A female subject 50 years old. The patient describes having a moderate number of moles. The patient says their skin reddens painfully with sun exposure. By self-report, no immunosuppression and no family history of skin cancer.
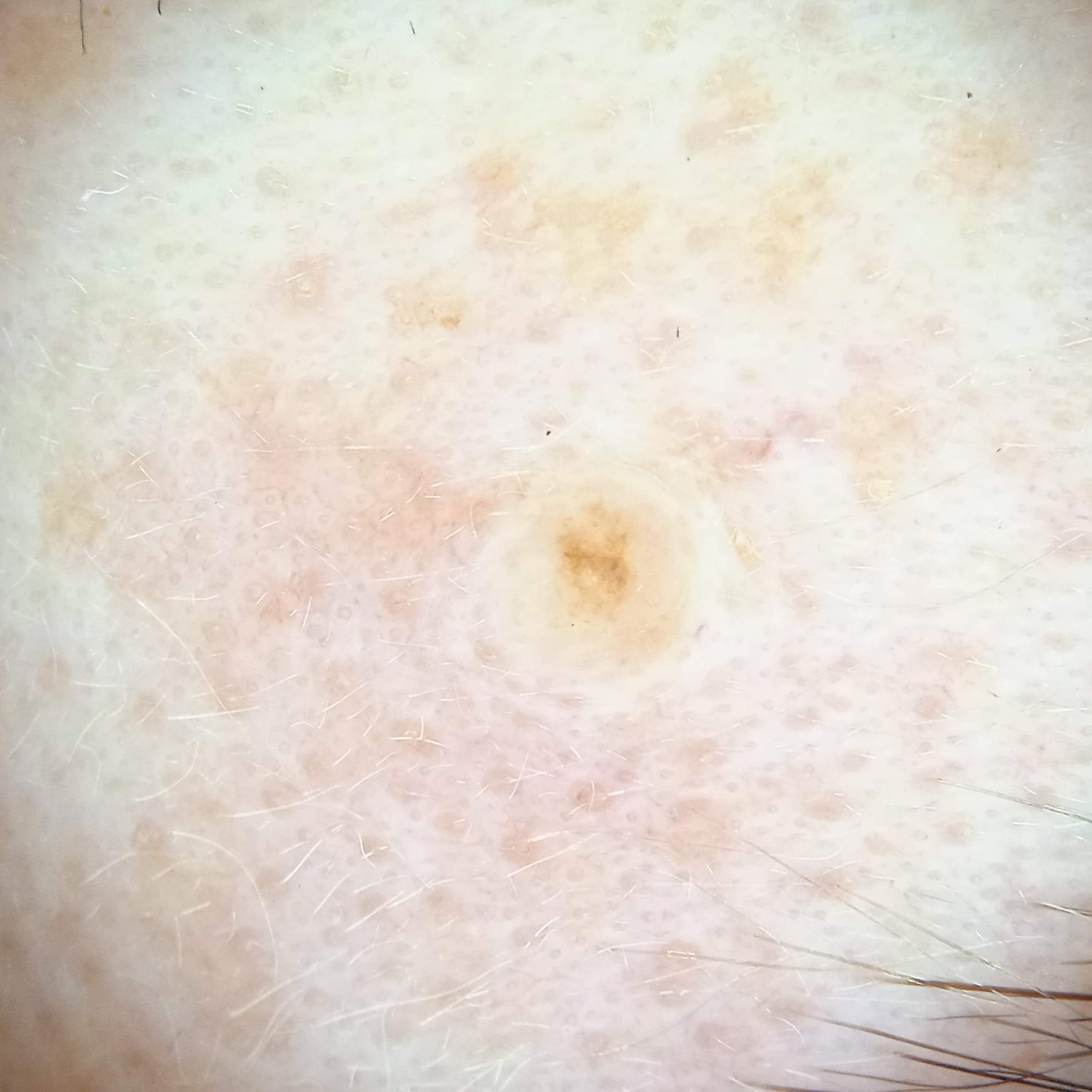Clinical context:
The lesion involves the face. Measuring roughly 1.8 mm.
Impression:
The dermatologists' assessment was a melanocytic nevus.